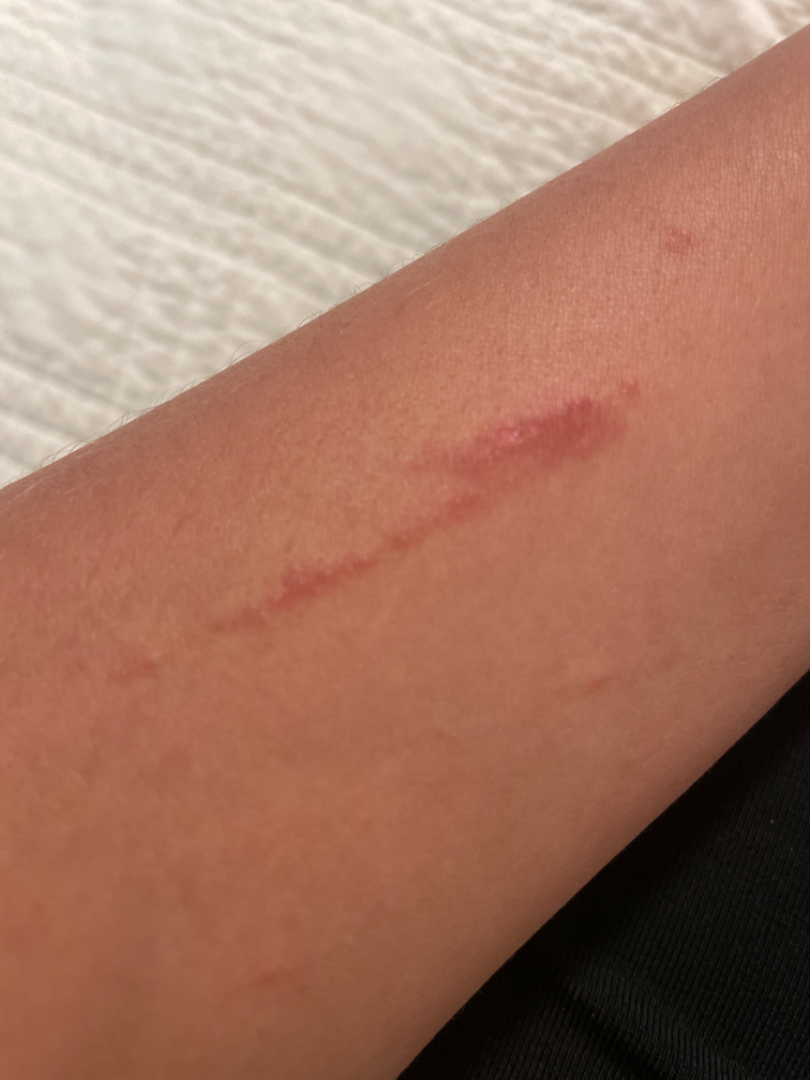History:
No associated systemic symptoms reported. Texture is reported as raised or bumpy. The lesion involves the arm. The patient considered this a rash. Close-up view. The condition has been present for less than one week.
Impression:
The leading consideration is Allergic Contact Dermatitis; also consider Contact dermatitis.